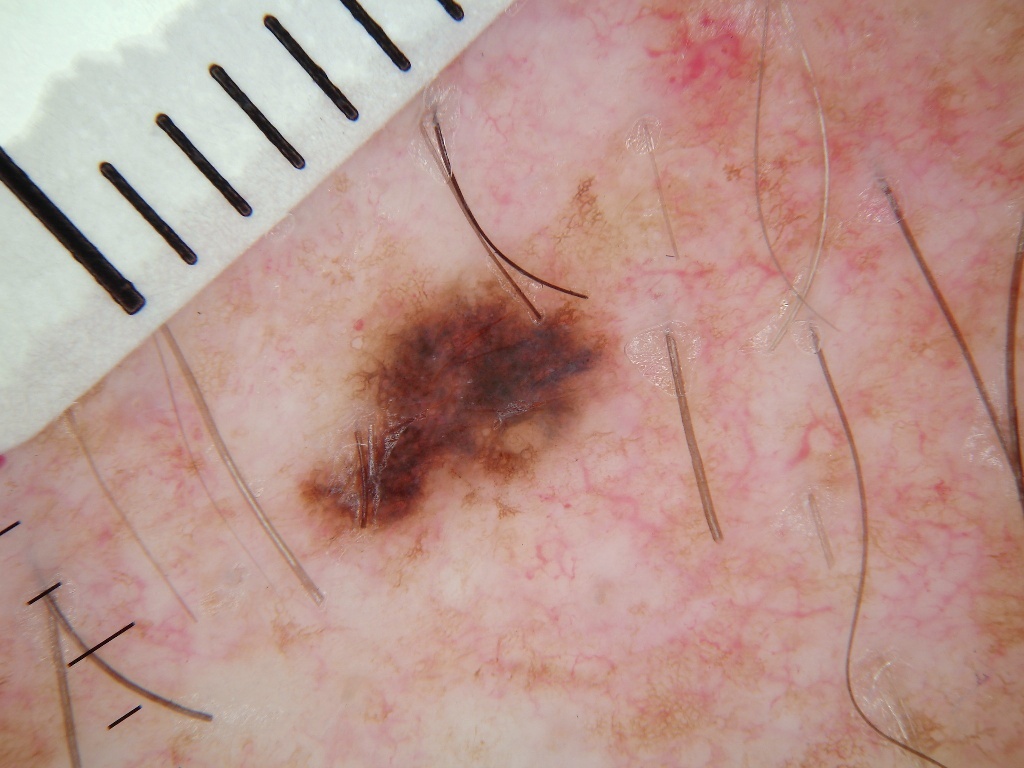A dermoscopic image of a skin lesion.
The lesion spans [289, 238, 632, 563].
The clinical diagnosis was a melanocytic nevus, a benign skin lesion.